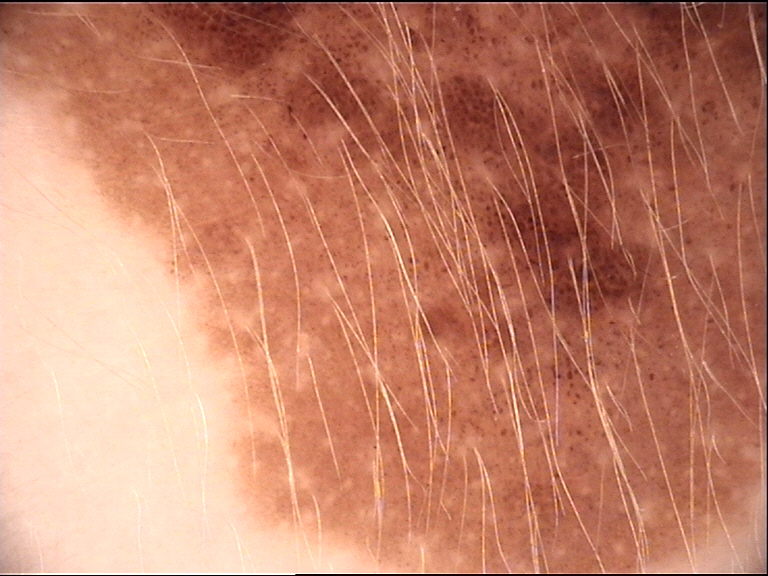modality: dermoscopy | lesion type: banal | assessment: congenital junctional nevus (expert consensus).